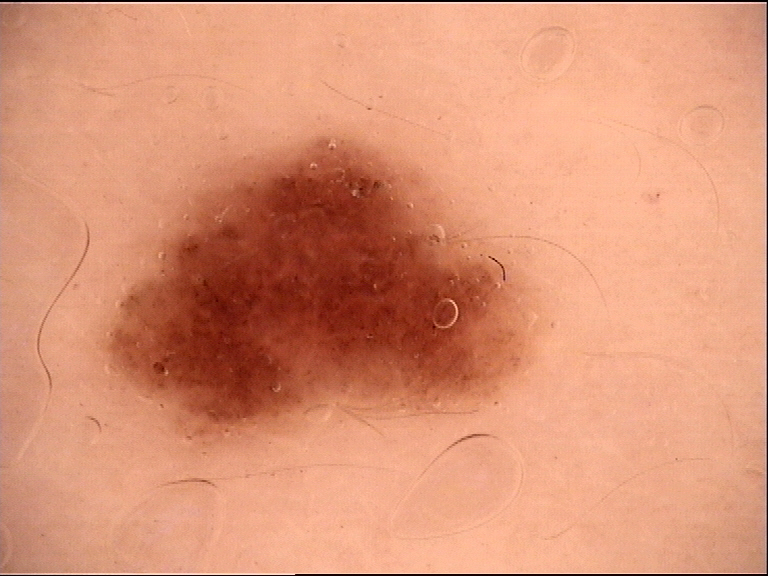Findings: A dermoscopic close-up of a skin lesion. Impression: The diagnostic label was a dysplastic junctional nevus.